The lesion involves the leg and top or side of the foot. Self-categorized by the patient as a rash. Present for less than one week. This image was taken at an angle. No associated lesion symptoms were reported. Skin tone: Fitzpatrick phototype IV; human graders estimated Monk Skin Tone 3 or 4. The contributor reports the lesion is rough or flaky — 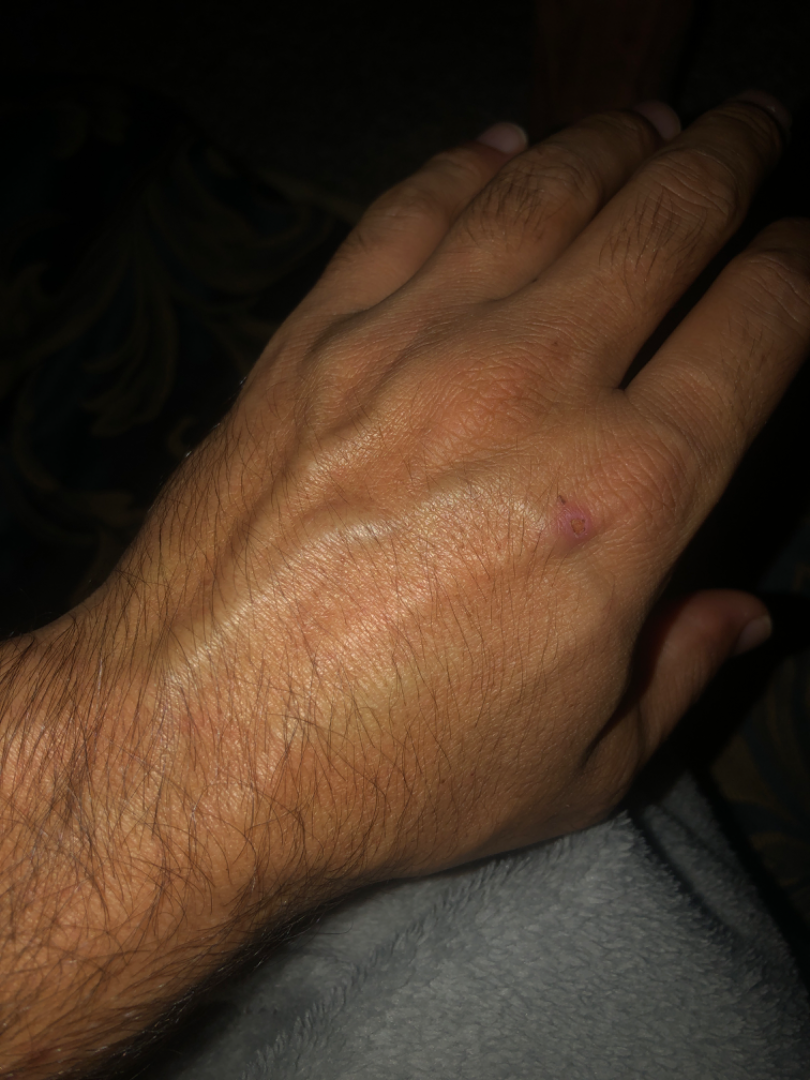On remote review of the image, the impression was split between Abrasion, scrape, or scab; Inflicted skin lesions; and Insect Bite.